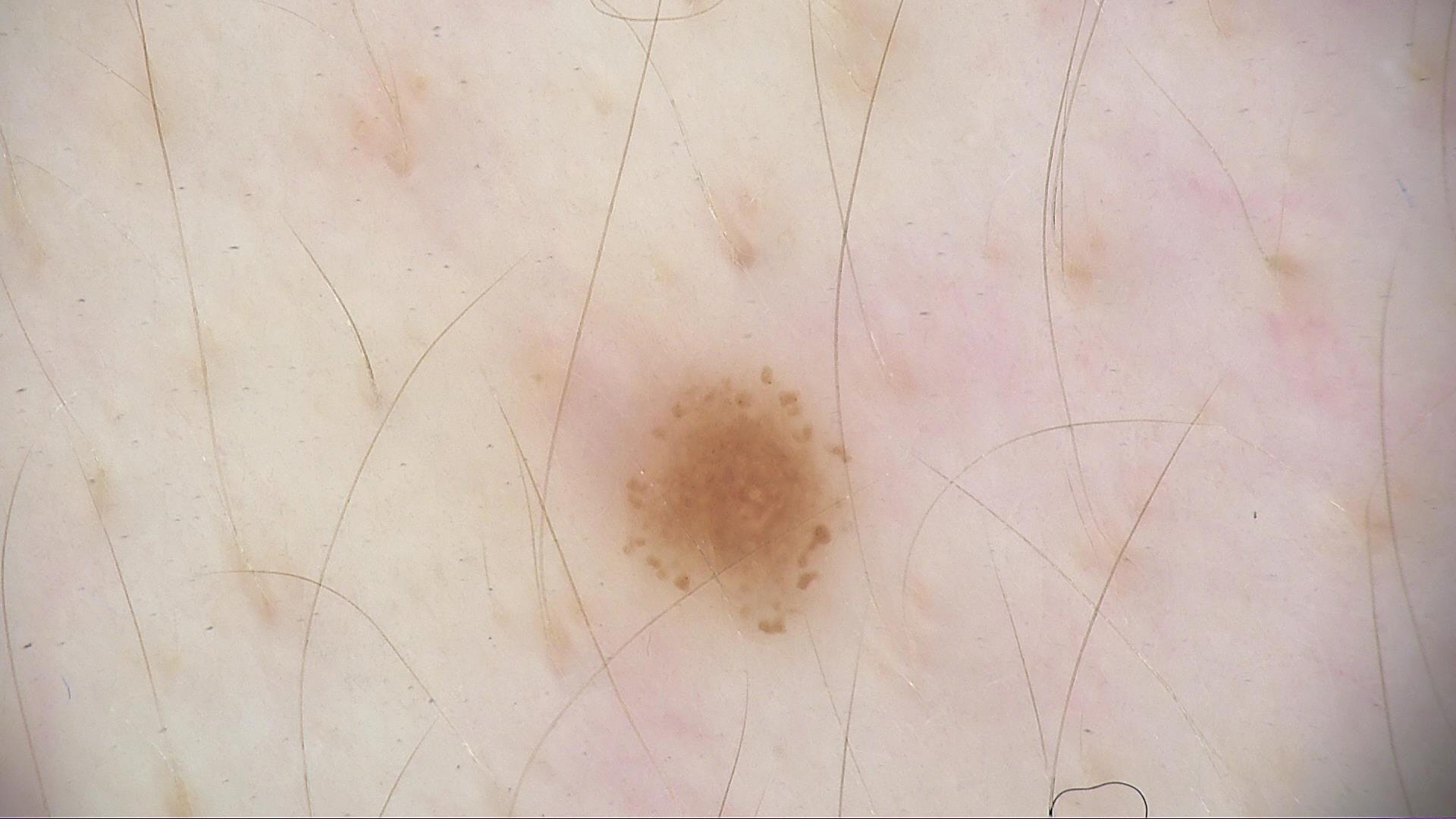modality = dermatoscopy
diagnosis = dysplastic junctional nevus (expert consensus)